A dermoscopic image of a skin lesion. The patient says their skin tans without first burning. Few moles overall by the patient's own estimate. On a questionnaire the patient reported a personal history of cancer:
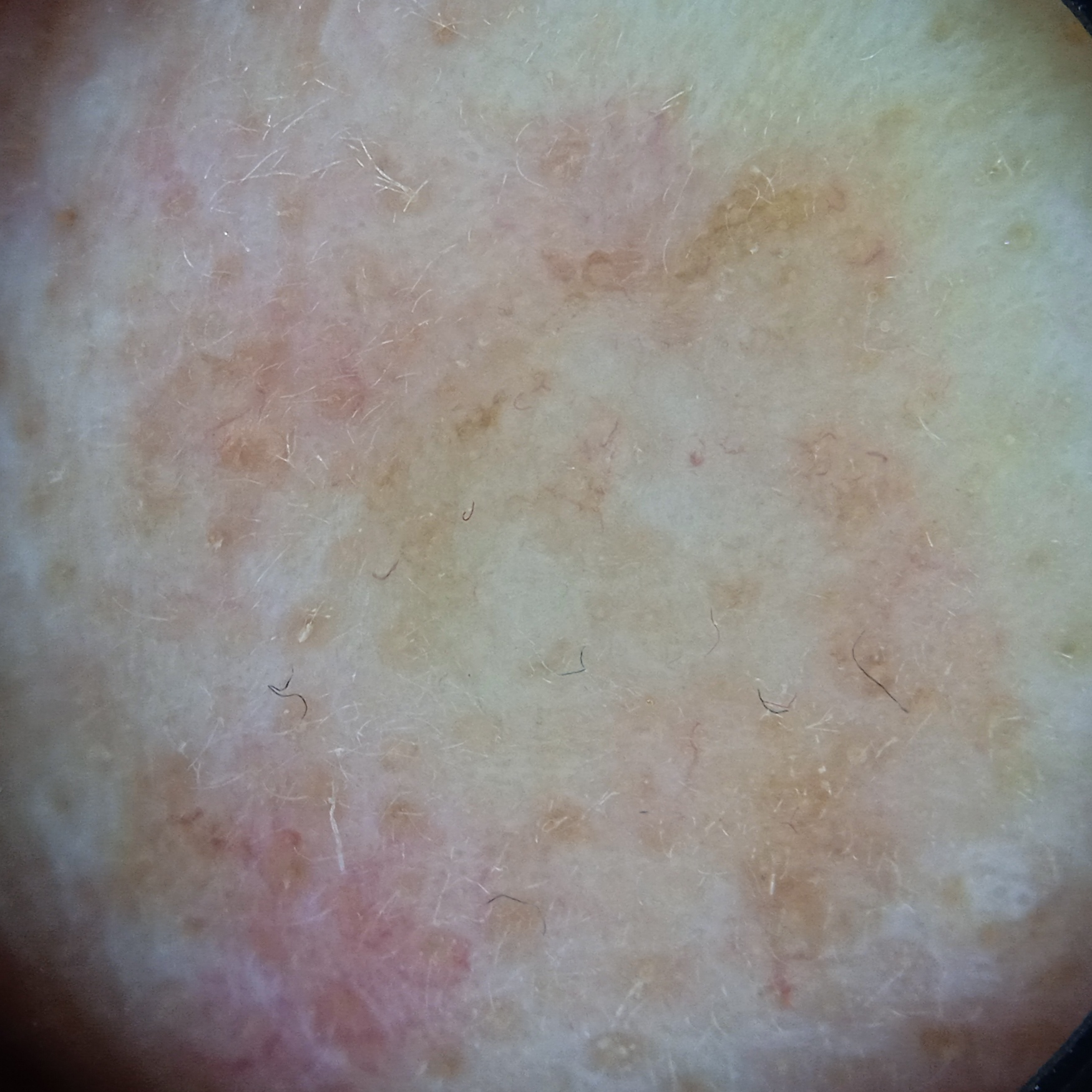Q: Where is the lesion?
A: the face
Q: What did the biopsy show?
A: basal cell carcinoma (biopsy-proven)